A dermatoscopic image of a skin lesion; the patient was assessed as Fitzpatrick skin type II; a female subject in their mid-30s — 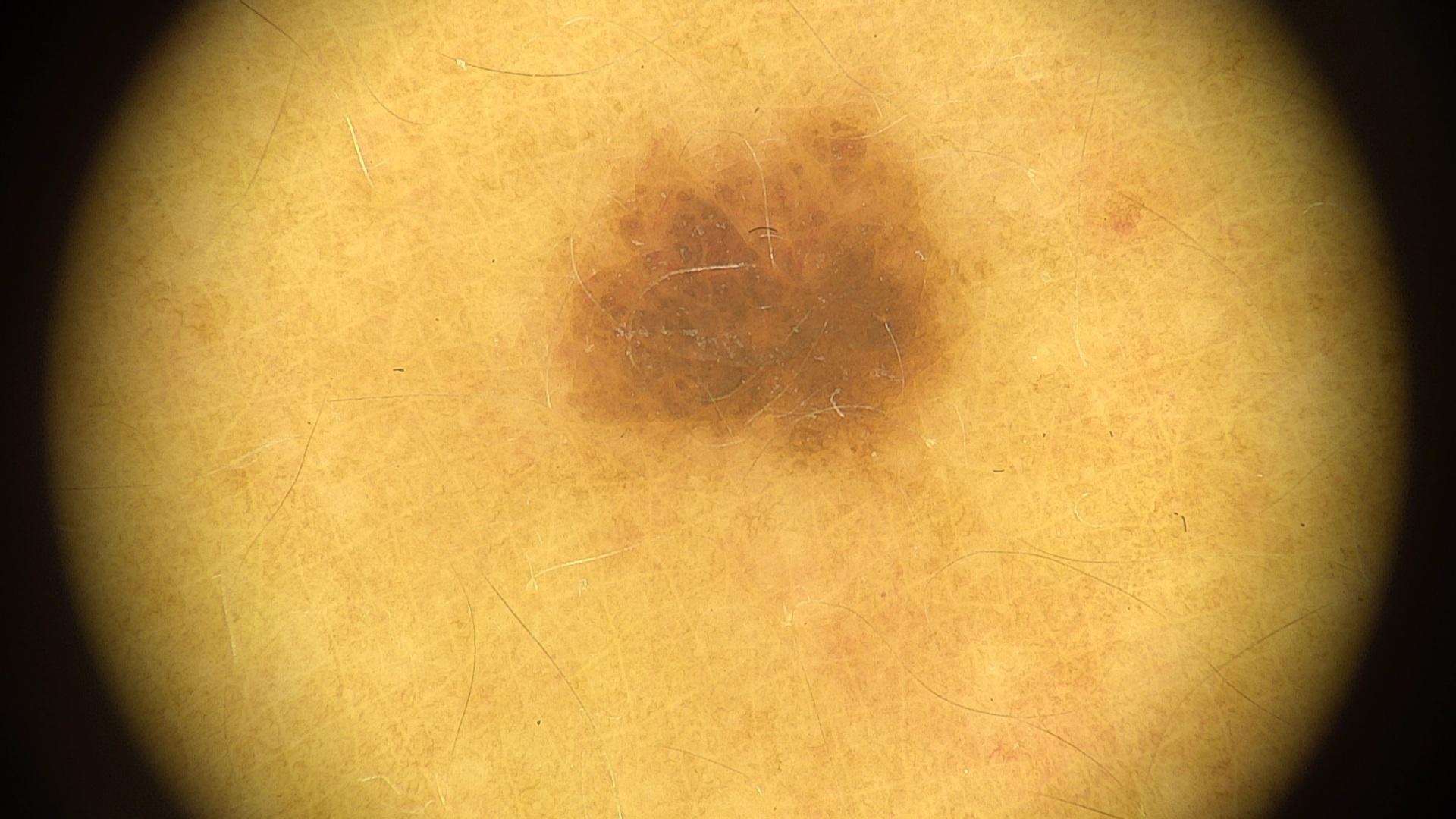Q: Where on the body is the lesion?
A: the trunk, specifically the posterior trunk
Q: What is the diagnosis?
A: Nevus (clinical impression)